A clinical photo of a skin lesion taken with a smartphone. The chart records pesticide exposure and prior skin cancer (patient or family). Fitzpatrick skin type III.
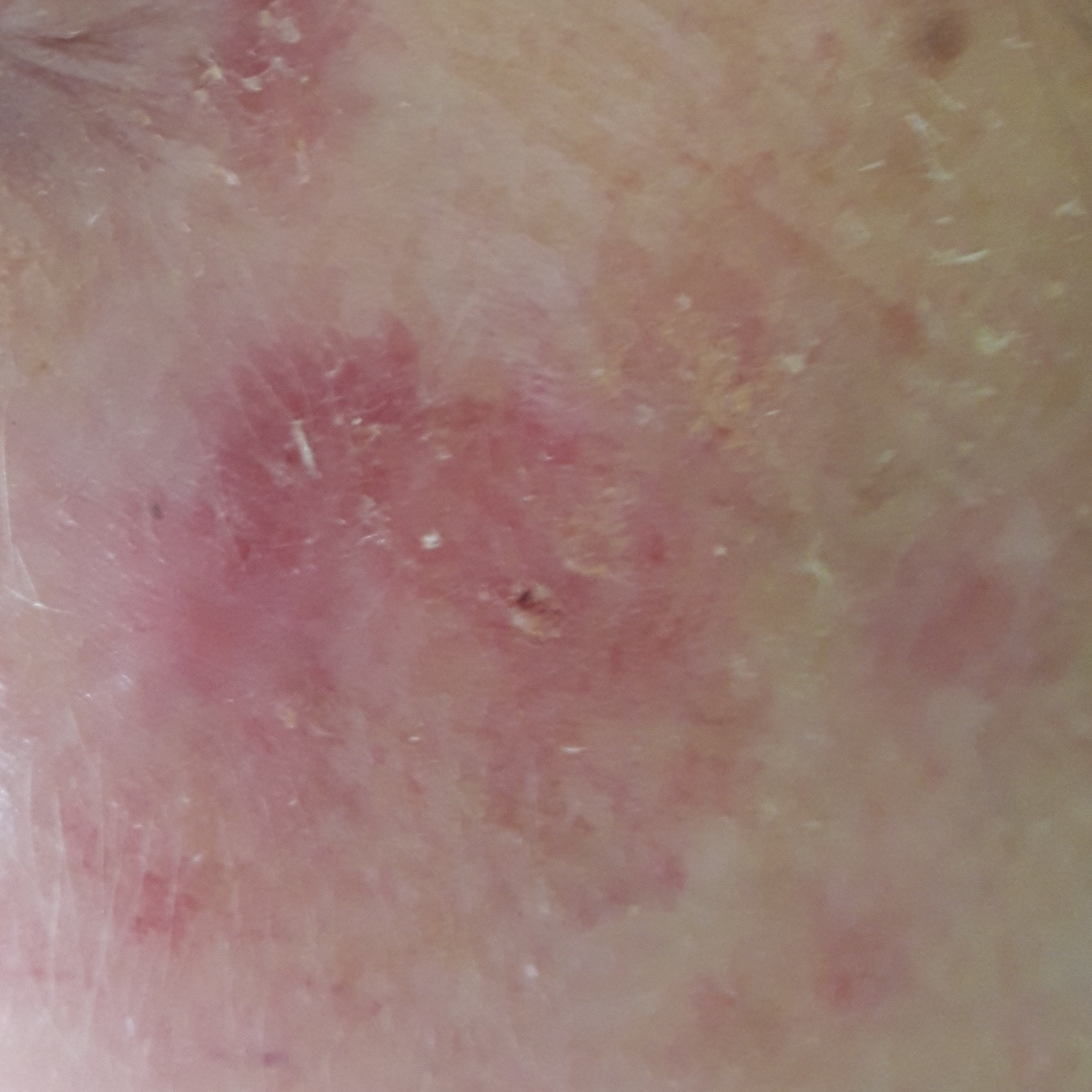The lesion is on the face. The lesion measures approximately 6 × 5 mm. Clinically diagnosed as a lesion of indeterminate malignant potential — an actinic keratosis.